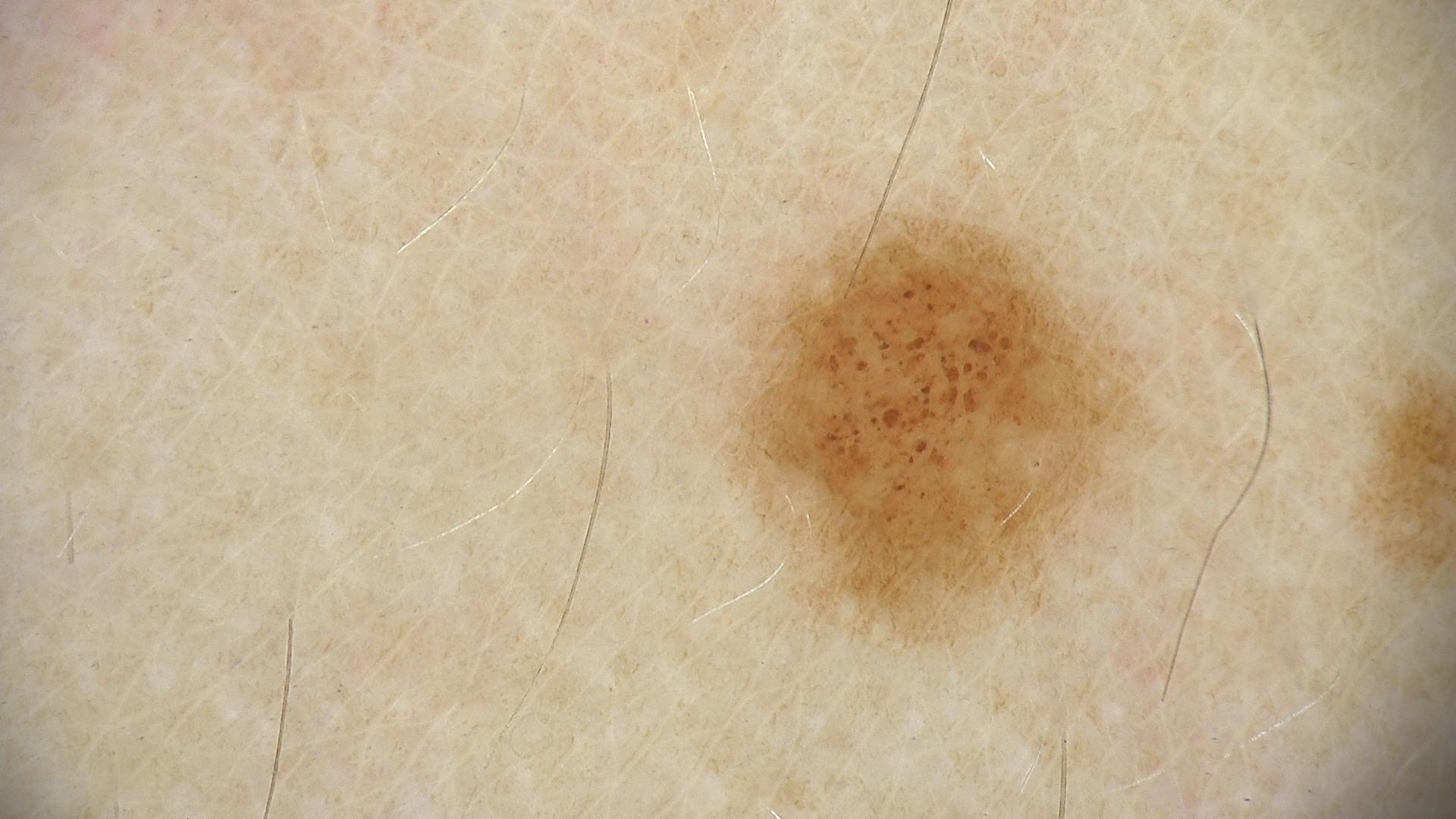Case:
* diagnostic label: dysplastic junctional nevus (expert consensus)